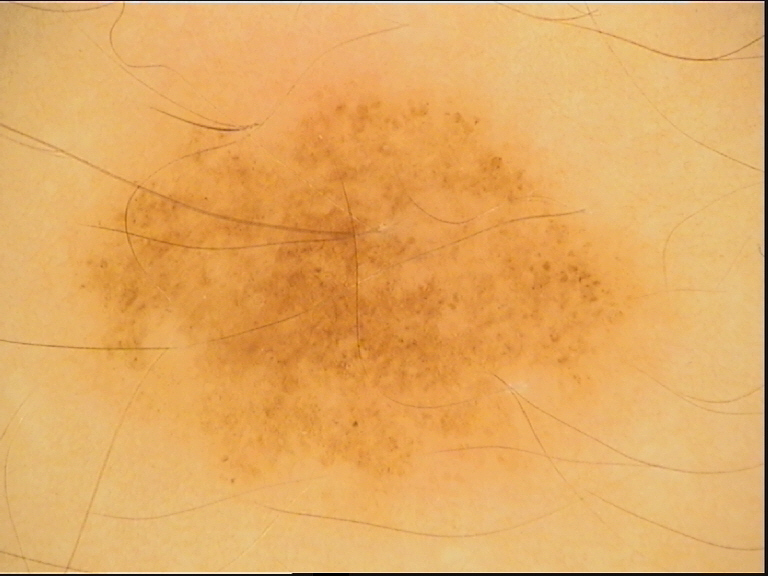Q: What is this lesion?
A: dysplastic junctional nevus (expert consensus)